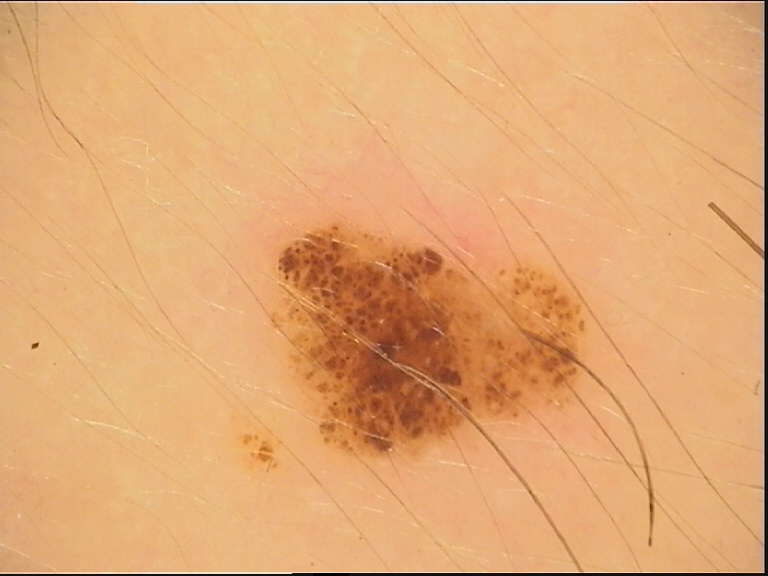A dermoscopic close-up of a skin lesion.
Classified as a banal lesion — a compound nevus.